This is a close-up image. The lesion involves the leg. The subject is 60–69, female.
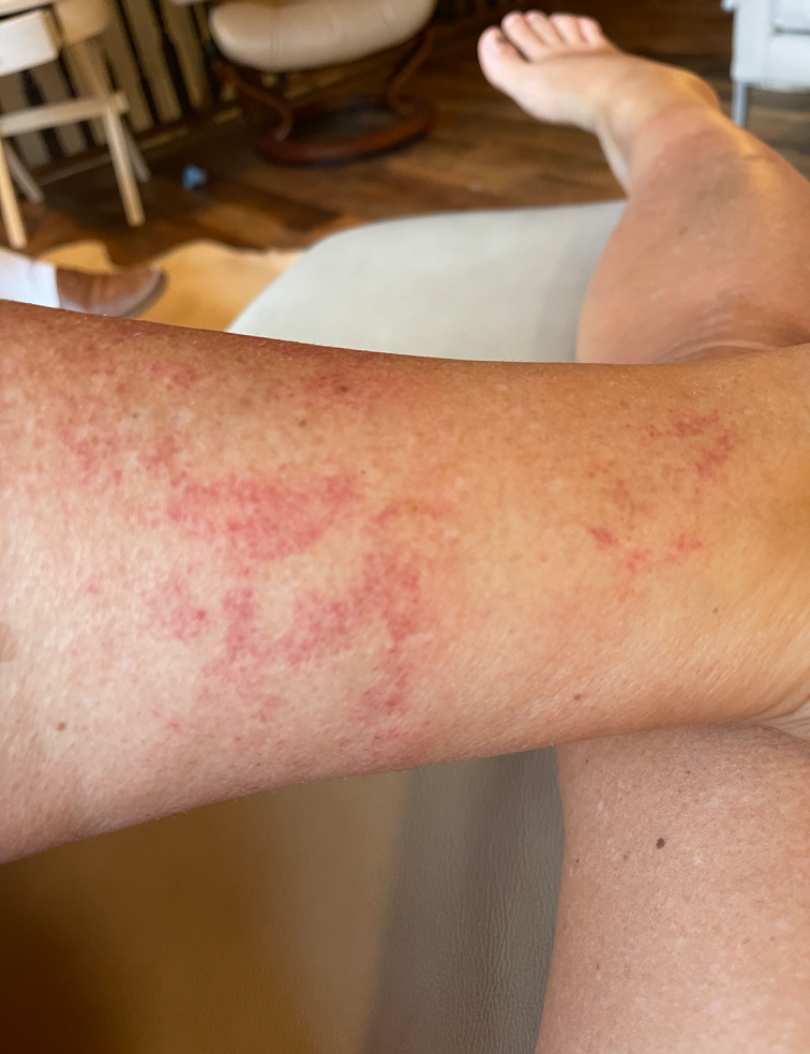Patient information:
The patient reports associated fatigue and joint pain. The patient reports bothersome appearance and enlargement. The patient described the issue as skin that appeared healthy to them. The patient reports the lesion is flat.
Review:
On remote dermatologist review, Pigmented purpuric eruption (most likely).